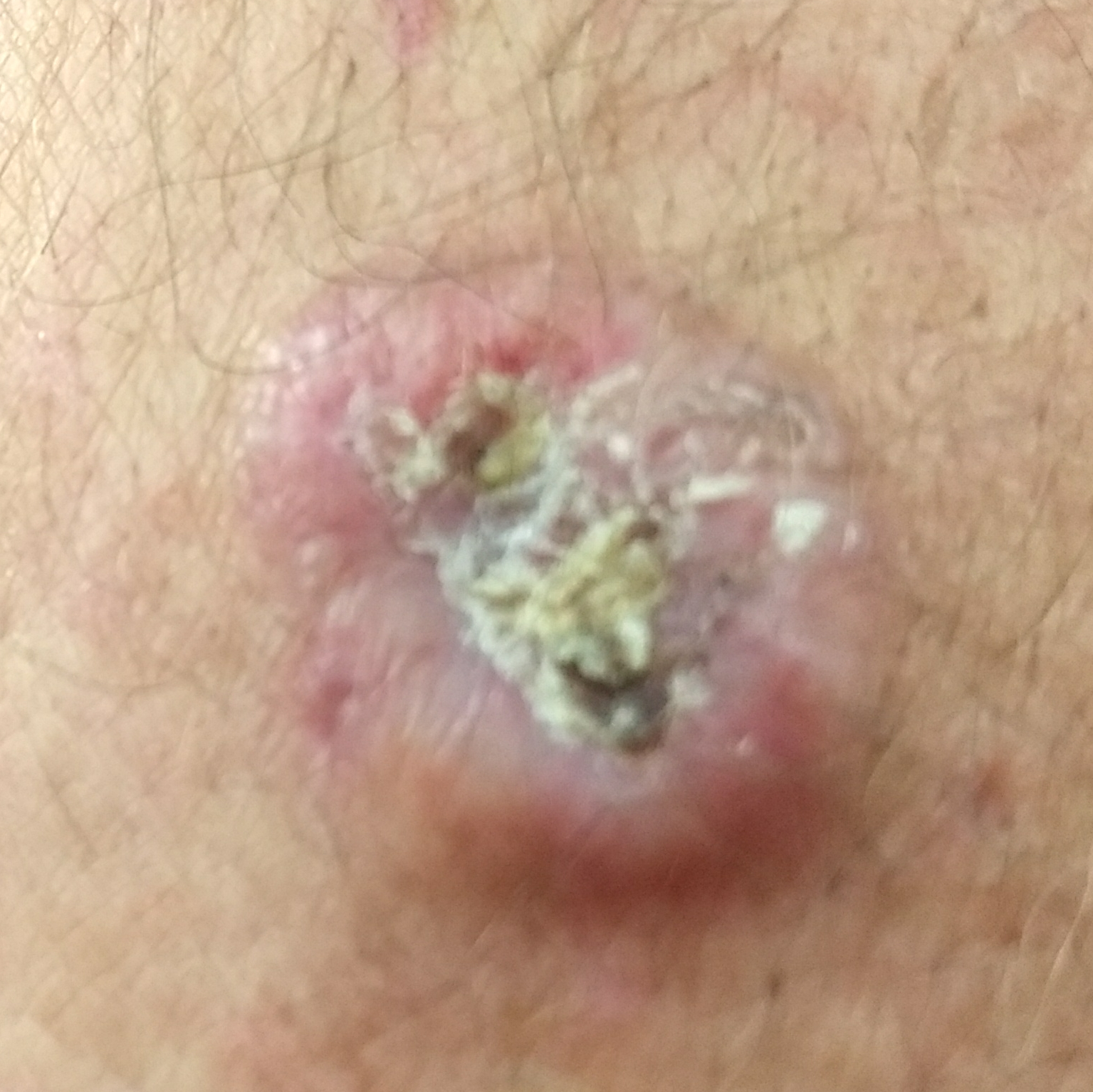{
  "diagnosis": {
    "name": "basal cell carcinoma",
    "code": "BCC",
    "malignancy": "malignant",
    "confirmation": "histopathology"
  }
}